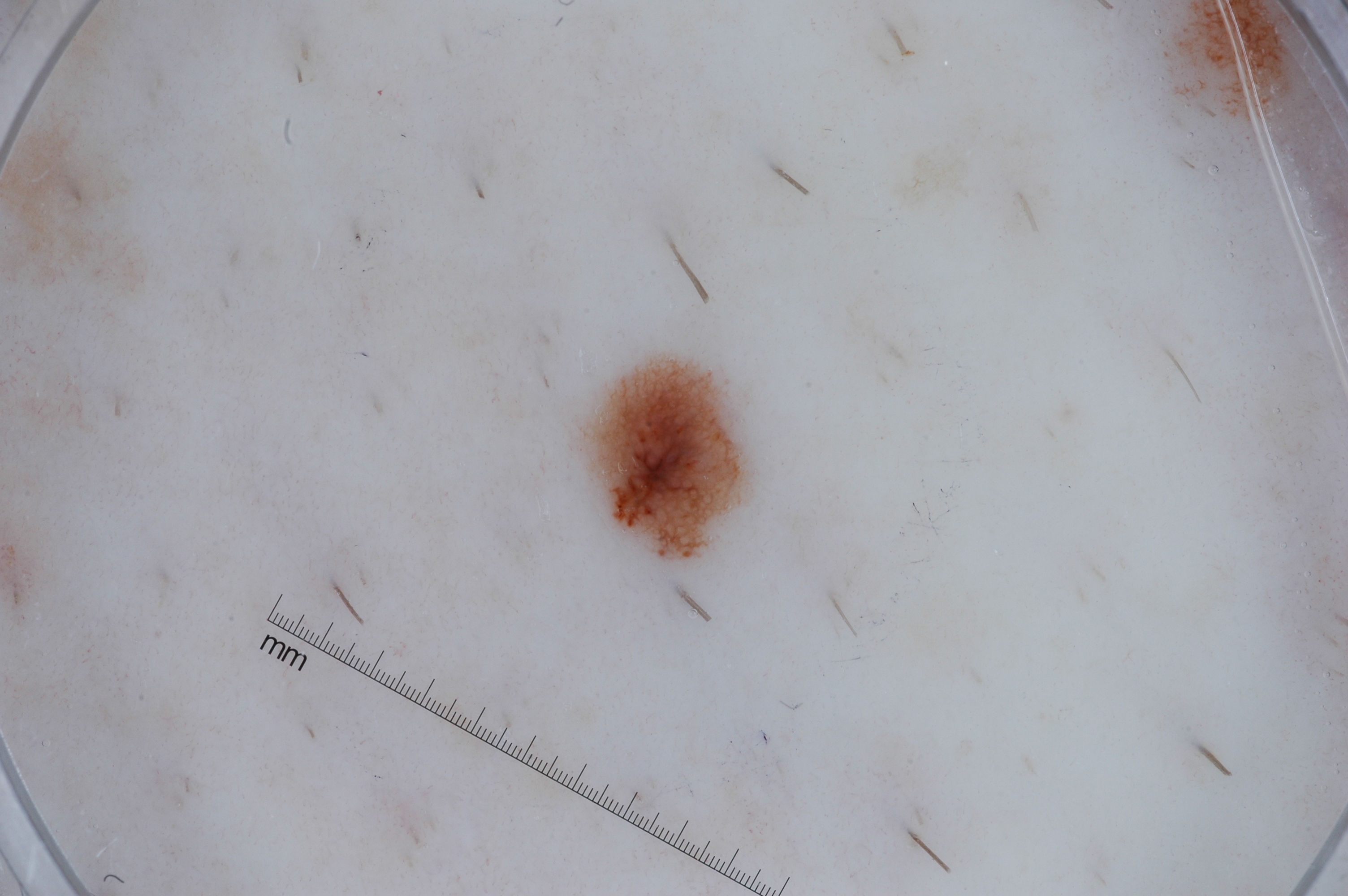A female patient aged approximately 40.
This is a dermoscopic photograph of a skin lesion.
The lesion occupies roughly 2% of the field.
On dermoscopy, the lesion shows pigment network; no milia-like cysts, streaks, or negative network.
The lesion spans bbox(590, 364, 747, 553).
Consistent with a melanocytic nevus, a benign skin lesion.